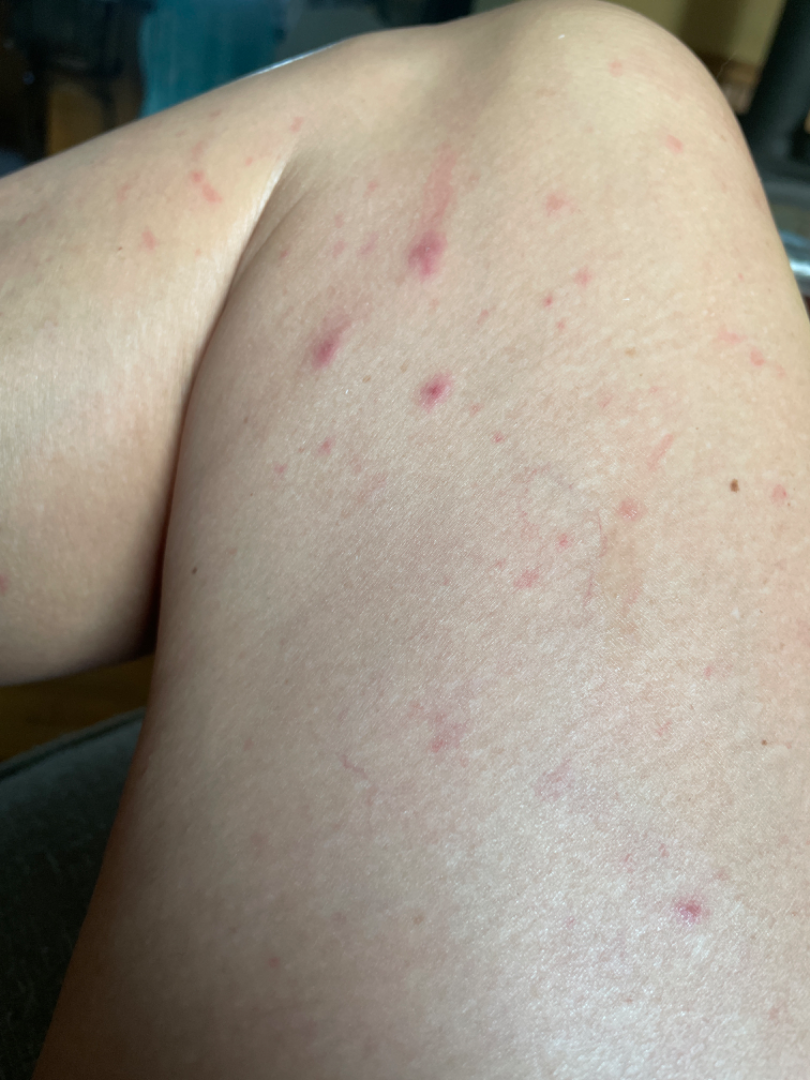Reviewed remotely by three dermatologists: the leading consideration is Folliculitis; less likely is Insect Bite; lower on the differential is Viral Exanthem.